Referred for assessment of suspected basal cell carcinoma; a female patient age 60; a dermoscopy image of a skin lesion:
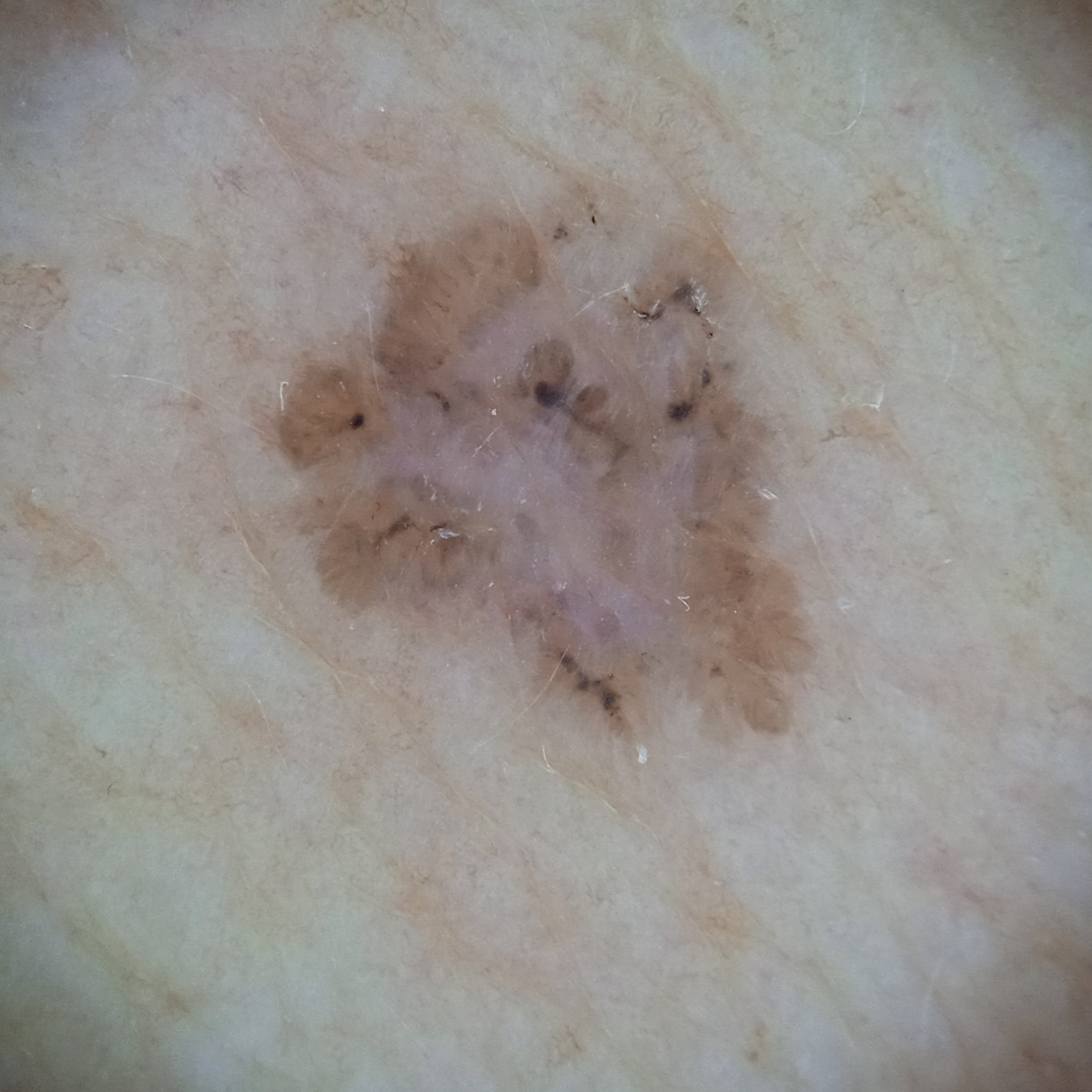lesion_size:
  diameter_mm: 7.2
diagnosis:
  name: basal cell carcinoma
  malignancy: malignant